The patient is a female aged 50–59; associated systemic symptoms include fatigue and joint pain; a close-up photograph; self-categorized by the patient as a rash; present for more than one year; the patient reports the lesion is raised or bumpy; the patient reports burning and pain; located on the head or neck; skin tone: non-clinician graders estimated Monk skin tone scale 2 (US pool) or 1 (India pool): 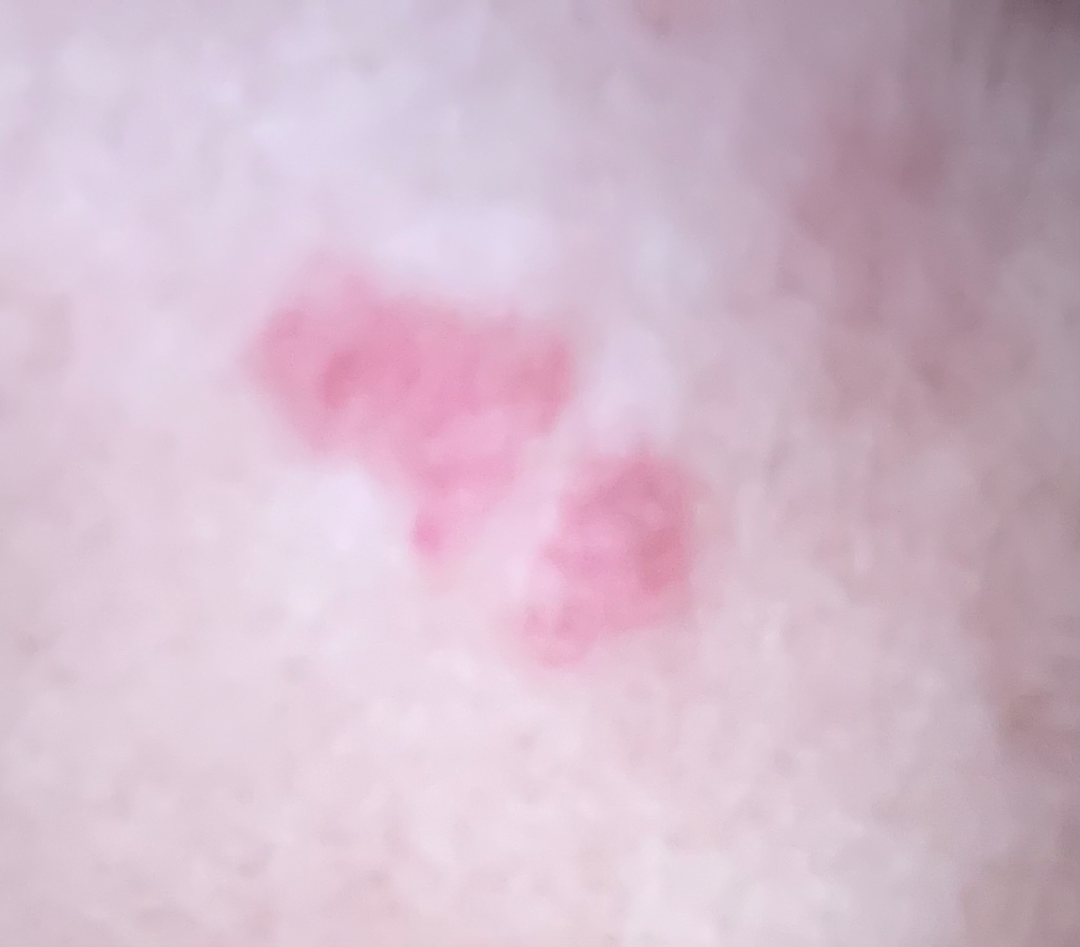The case was difficult to assess from the available photograph.